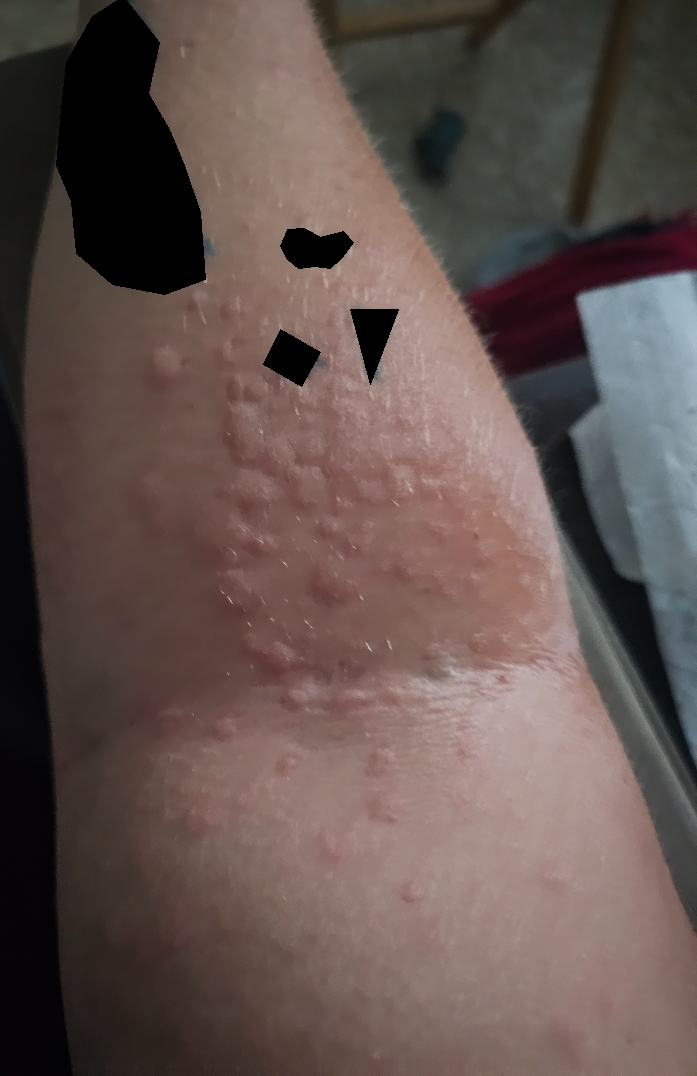Clinical context: Fitzpatrick IV. This image was taken at a distance. Assessment: Reviewed remotely by one dermatologist: consistent with Urticaria.